The photo was captured at a distance:
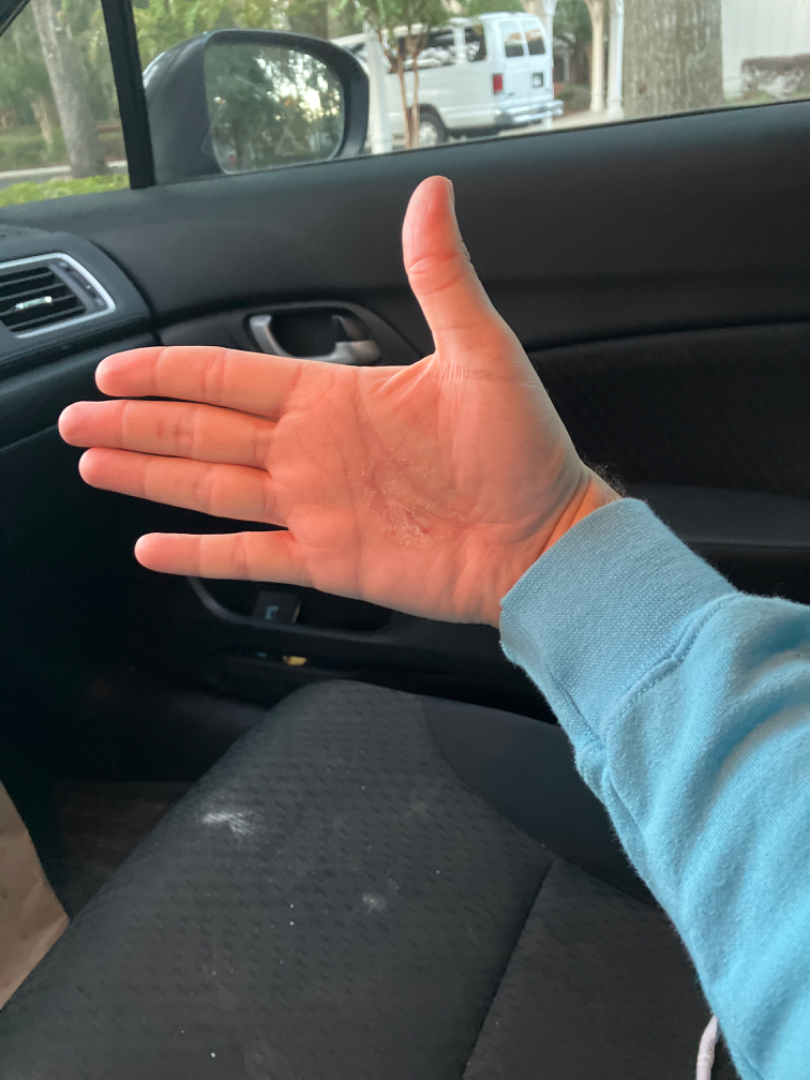Single-reviewer assessment: most likely Psoriasis; with consideration of Eczema; also raised was Allergic Contact Dermatitis.